A dermoscopy image of a single skin lesion:
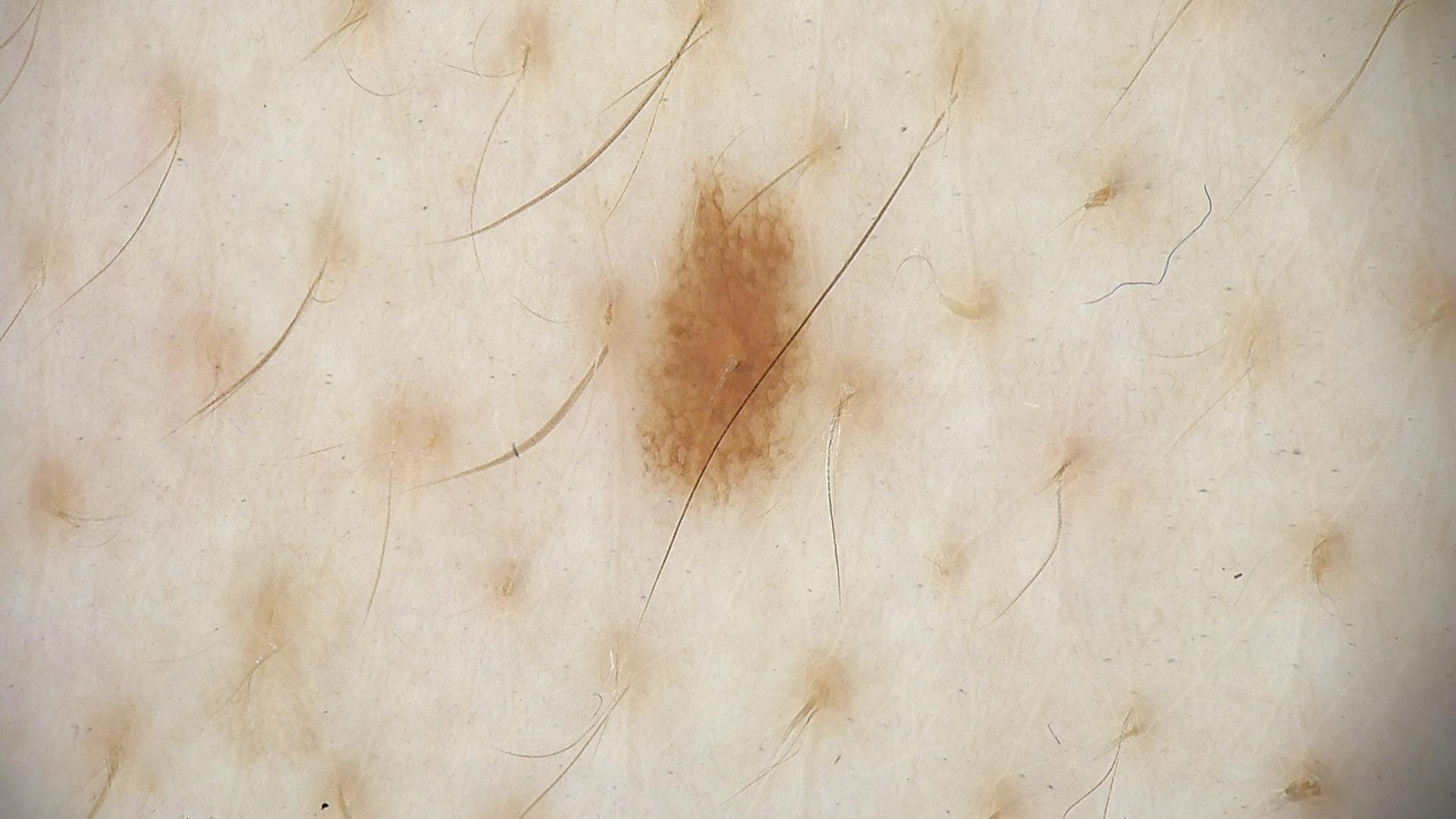The diagnosis was a benign lesion — a dysplastic junctional nevus.